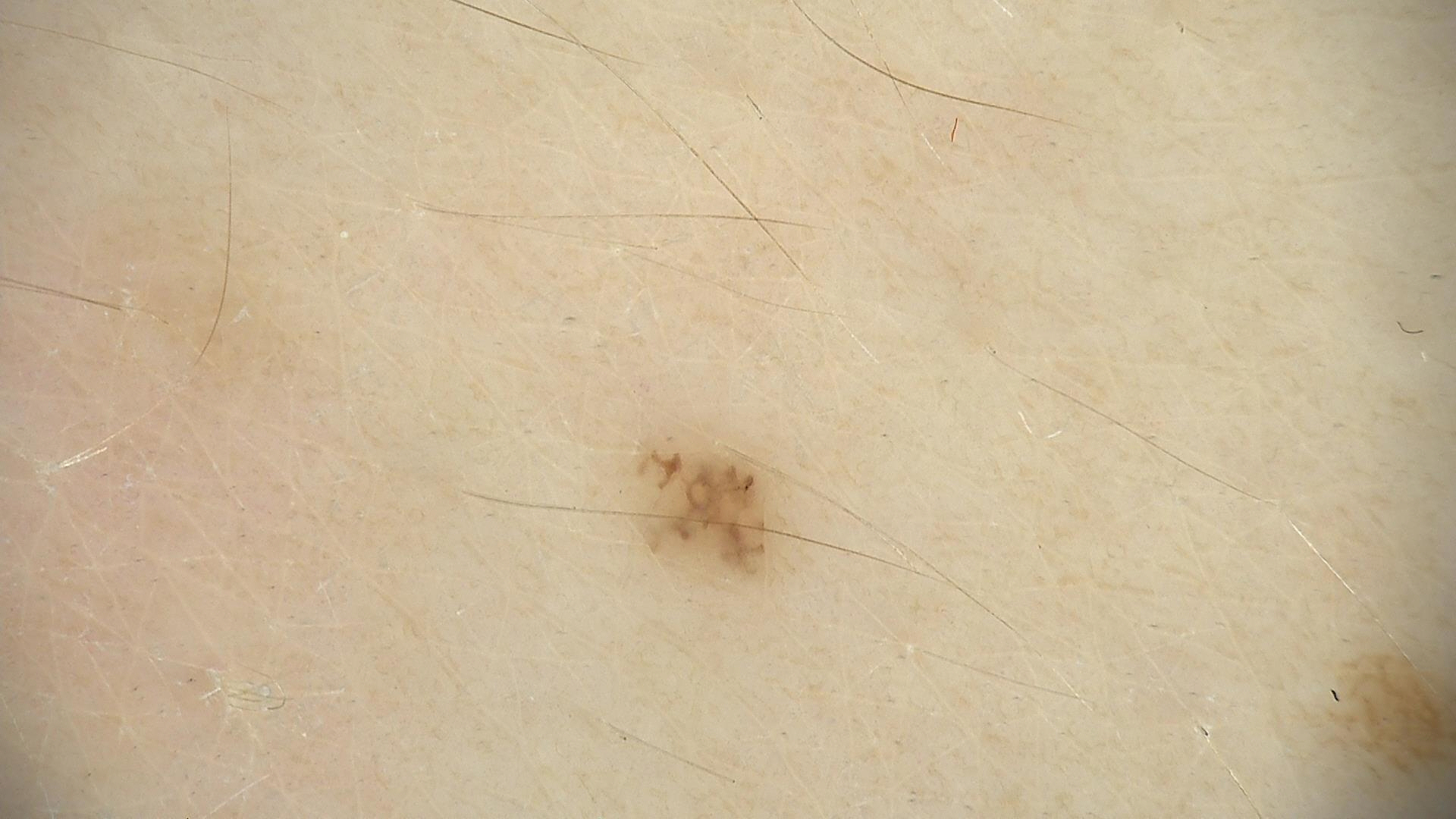Classified as a benign lesion — a dysplastic junctional nevus.